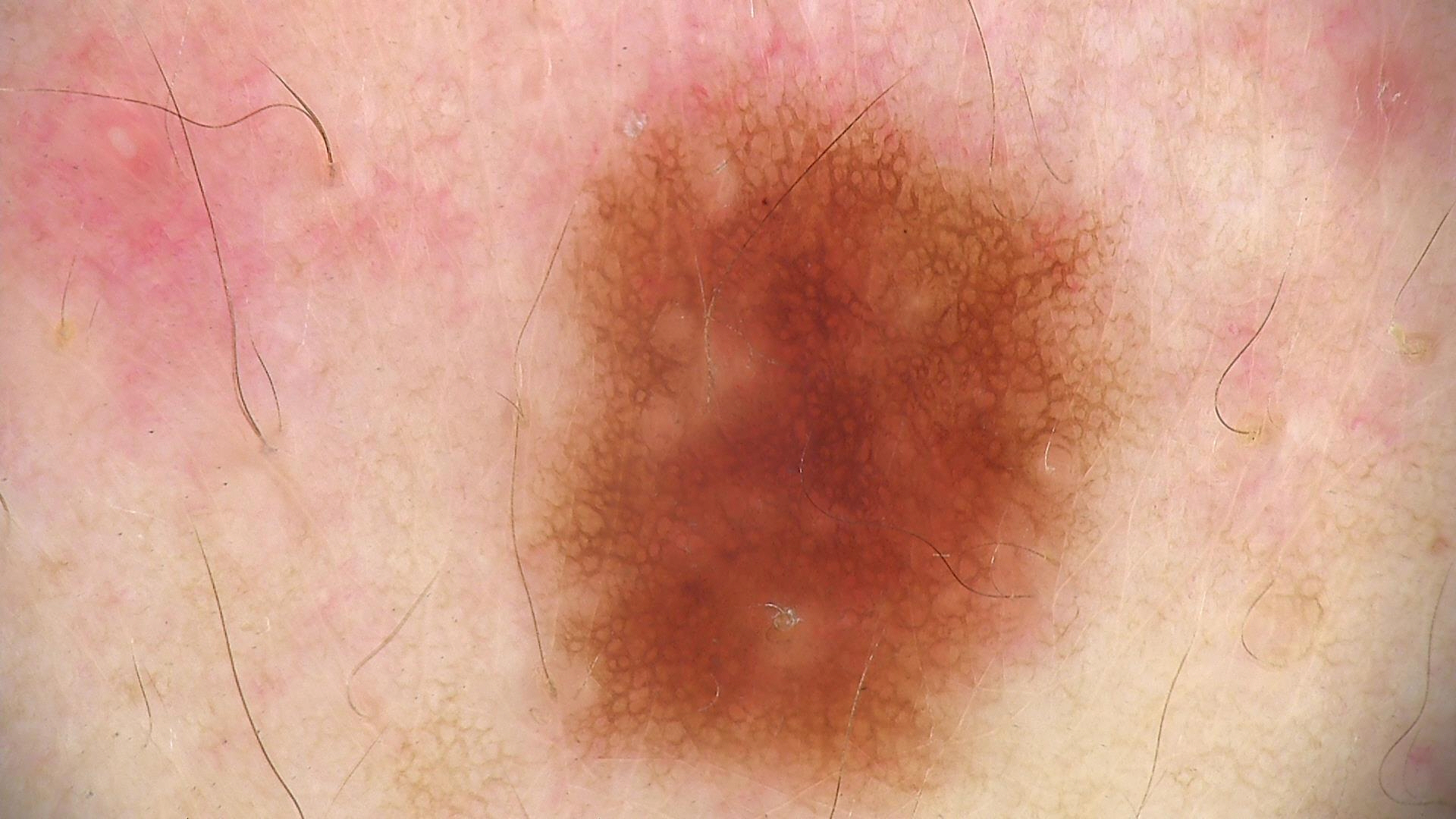Classified as a dysplastic junctional nevus.